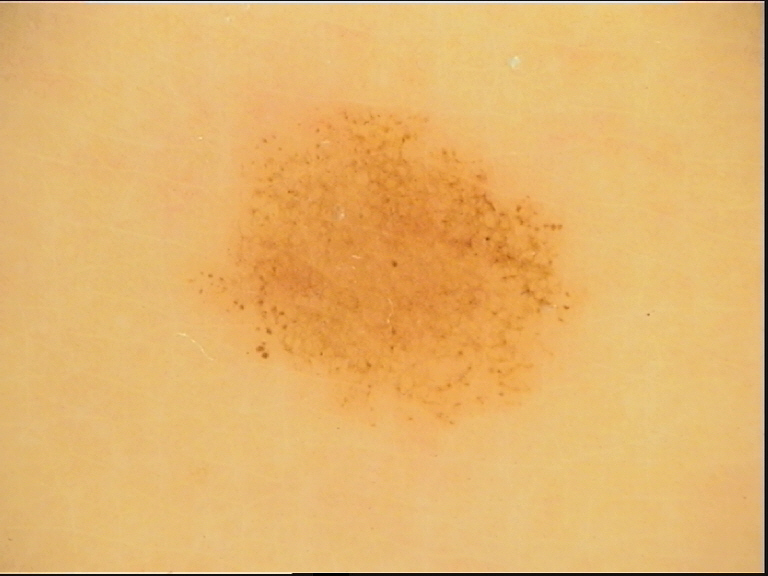Summary: A dermoscopy image of a single skin lesion. Impression: The diagnostic label was a benign lesion — a dysplastic junctional nevus.